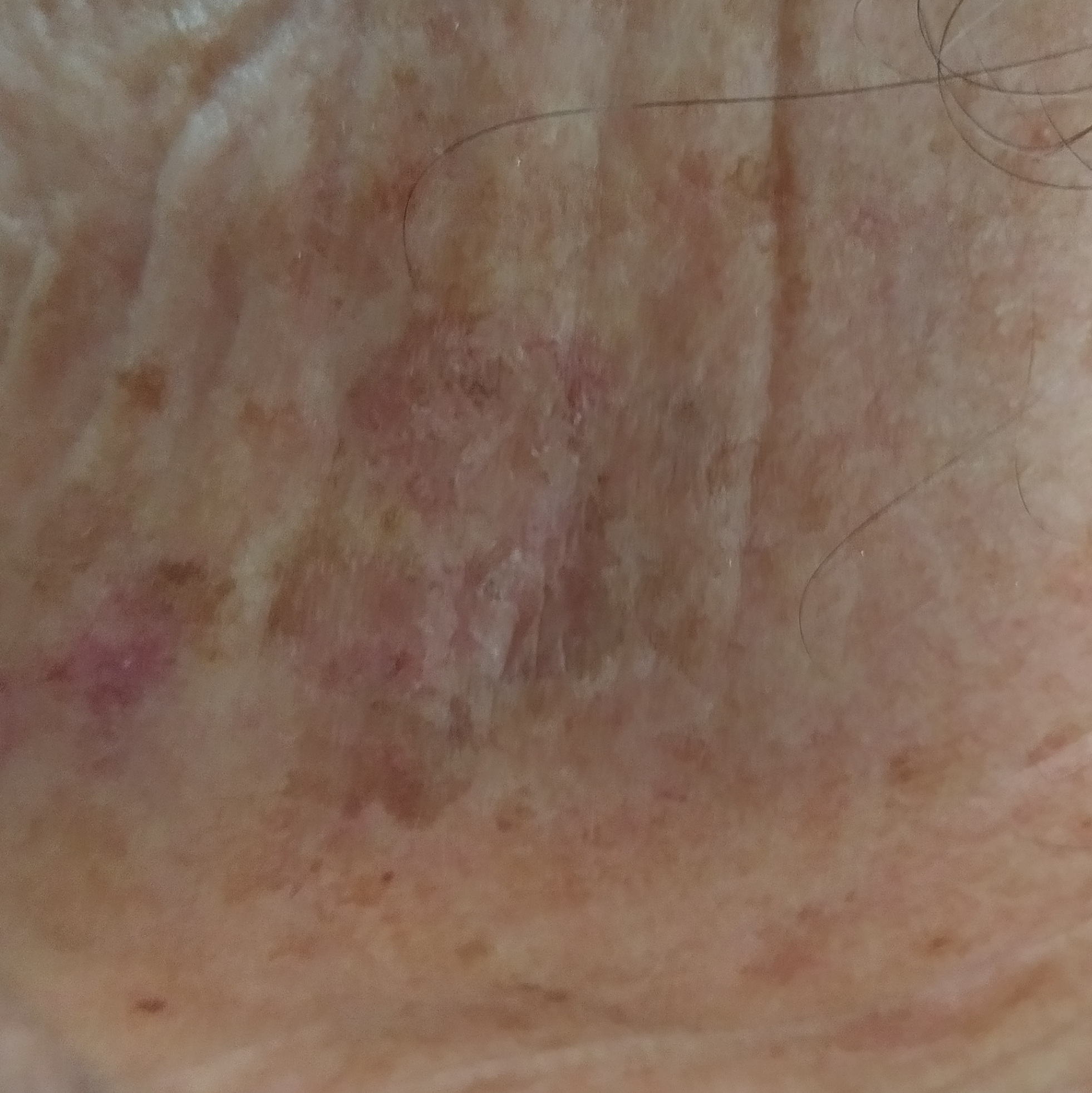Summary: A patient in their 60s. A clinical photo of a skin lesion taken with a smartphone. The lesion was found on the face. Asymptomatic by report. Conclusion: The consensus clinical diagnosis was a premalignant lesion — an actinic keratosis.